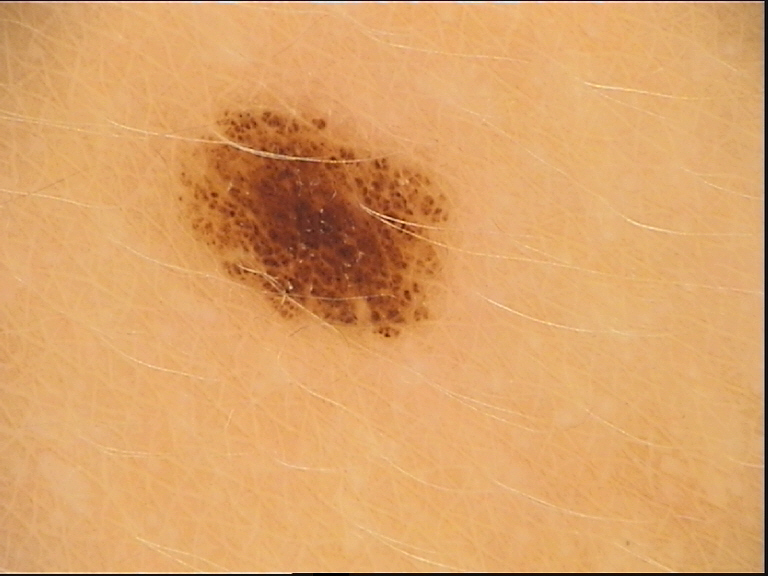Dermoscopy of a skin lesion.
The architecture is that of a banal lesion.
The diagnosis was a compound nevus.